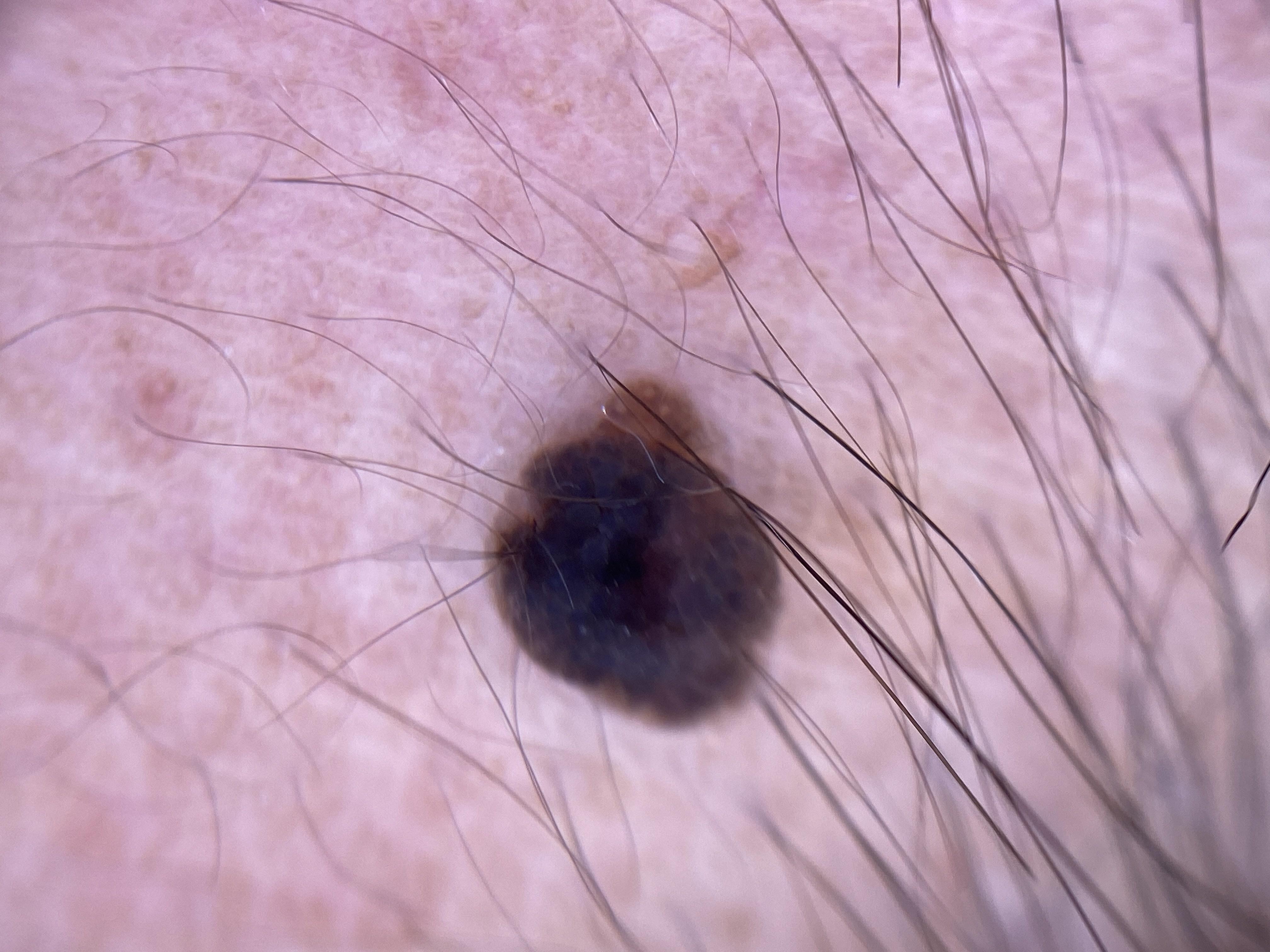A male subject in their 40s.
A contact-polarized dermoscopy image of a skin lesion.
On biopsy, the diagnosis was a nevus.